Located on the head or neck and arm; an image taken at an angle — 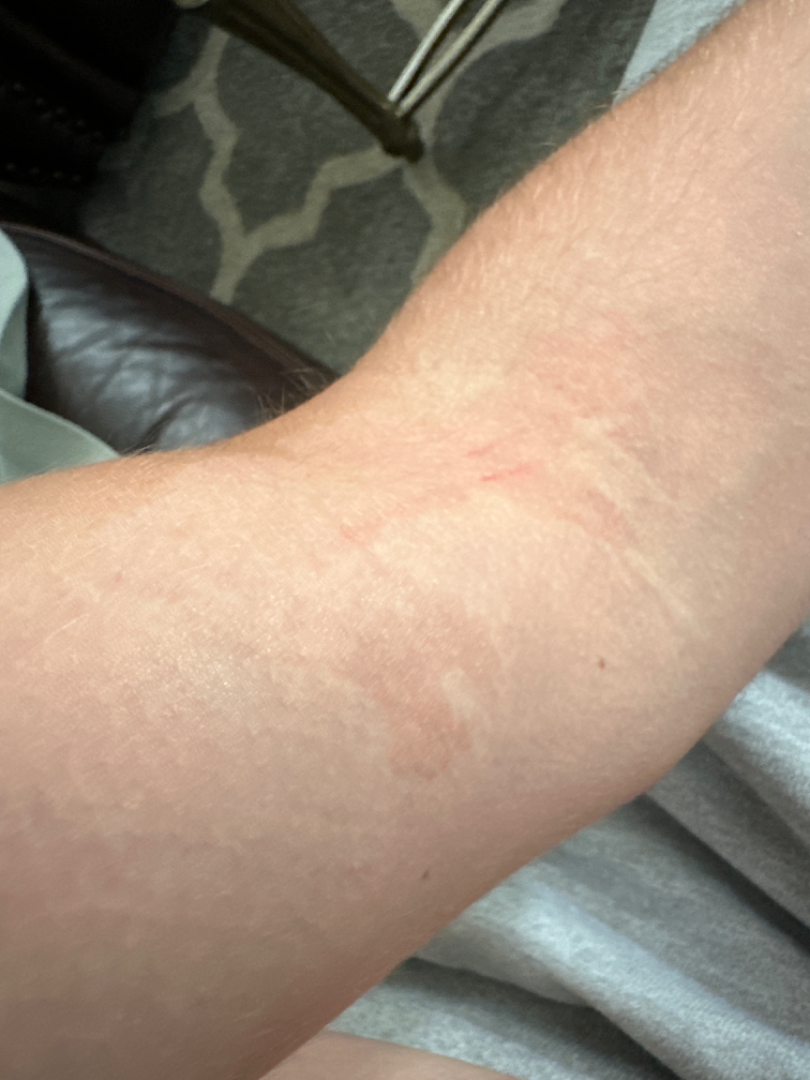assessment = could not be assessed.